The lesion is described as raised or bumpy and fluid-filled. A close-up photograph. The lesion involves the arm and leg. The patient indicates bothersome appearance, bleeding and pain. The patient indicates the condition has been present for one to three months. The patient reported no systemic symptoms. The subject is male: 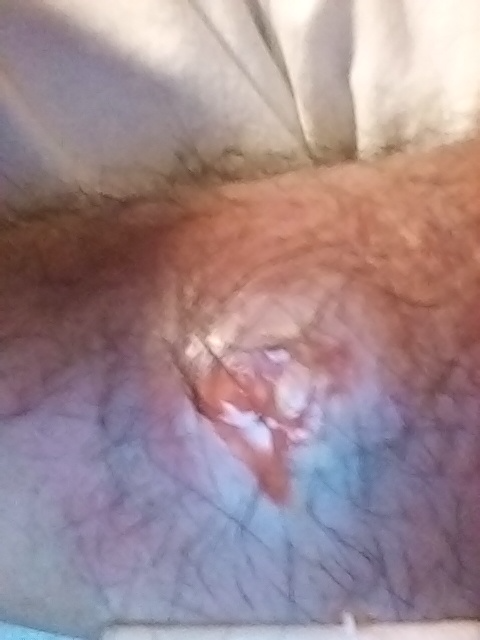Assessment: The dermatologist could not determine a likely condition from the photograph alone.